A close-up photograph — 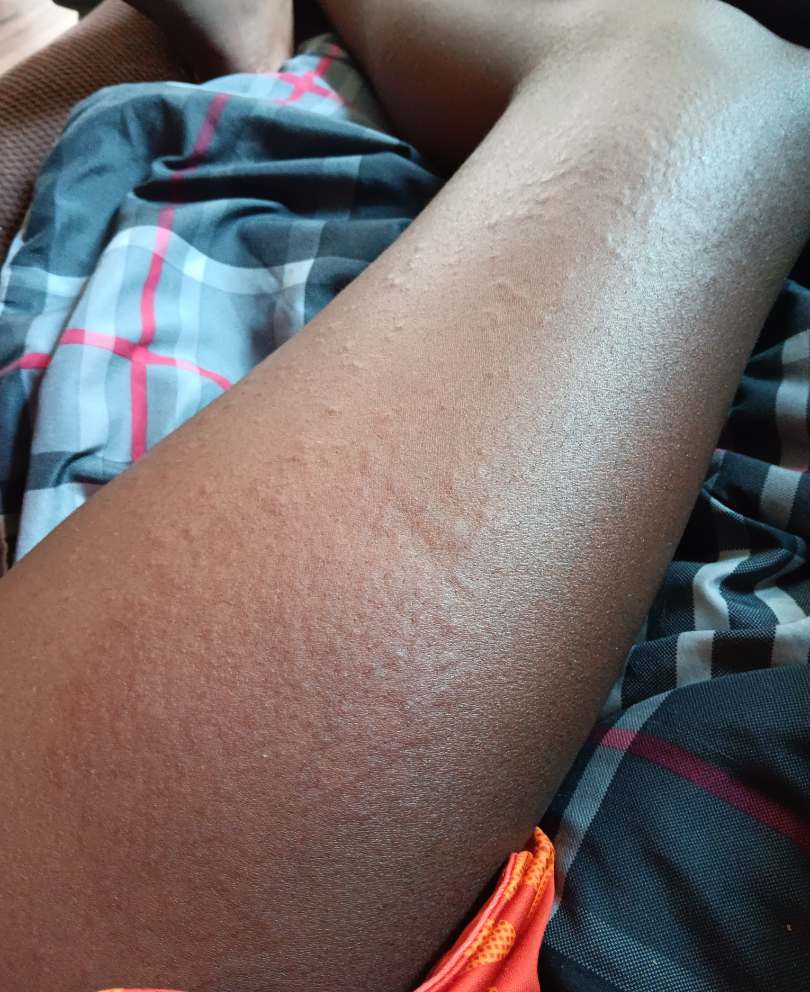| key | value |
|---|---|
| assessment | indeterminate |
| patient-reported symptoms | itching |
| self-categorized as | a rash |
| skin tone | FST VI; non-clinician graders estimated Monk Skin Tone 7 (US pool) or 4 (India pool) |